The contributor notes the lesion is rough or flaky · the patient described the issue as a pigmentary problem · no relevant lesion symptoms reported · located on the arm and front of the torso · the photo was captured at a distance — 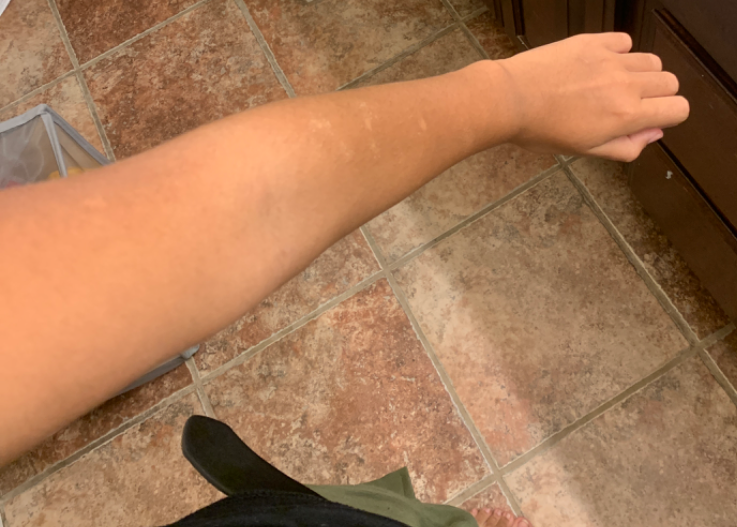The image was not sufficient for the reviewer to characterize the skin condition.